The subject is a female aged 40–49, located on the arm, an image taken at a distance.
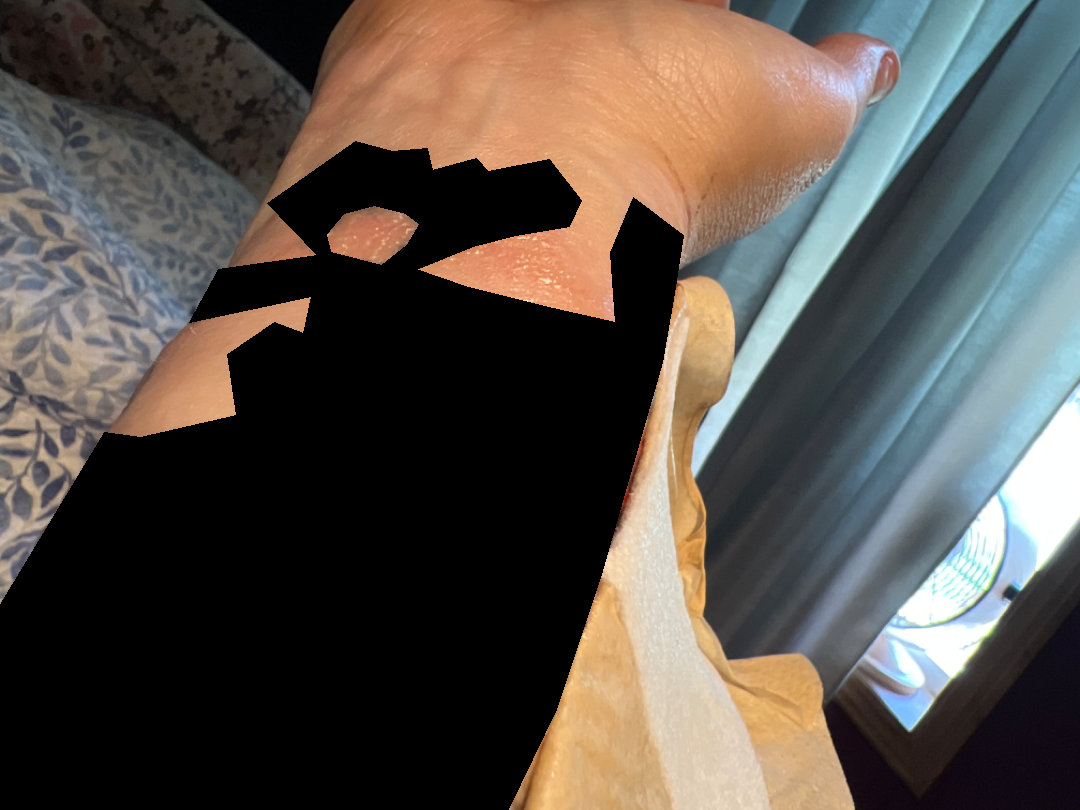Q: How long has this been present?
A: one to four weeks
Q: What symptoms does the patient report?
A: burning, enlargement, bothersome appearance and itching
Q: Texture?
A: fluid-filled and raised or bumpy
Q: What conditions are considered?
A: Allergic Contact Dermatitis (55%); Herpes Zoster (27%); Impetigo (18%)